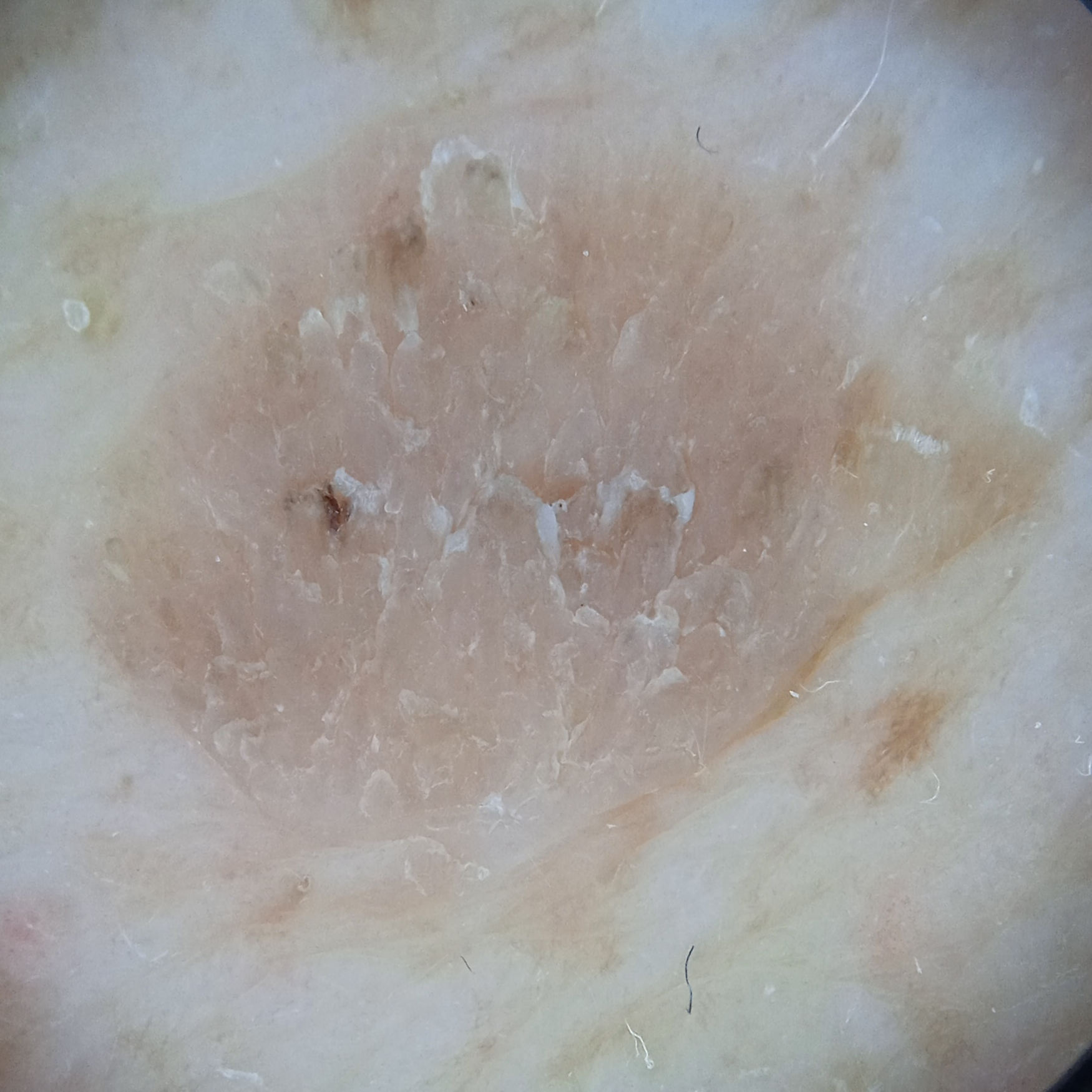{
  "diagnosis": {
    "name": "seborrheic keratosis",
    "malignancy": "benign"
  }
}